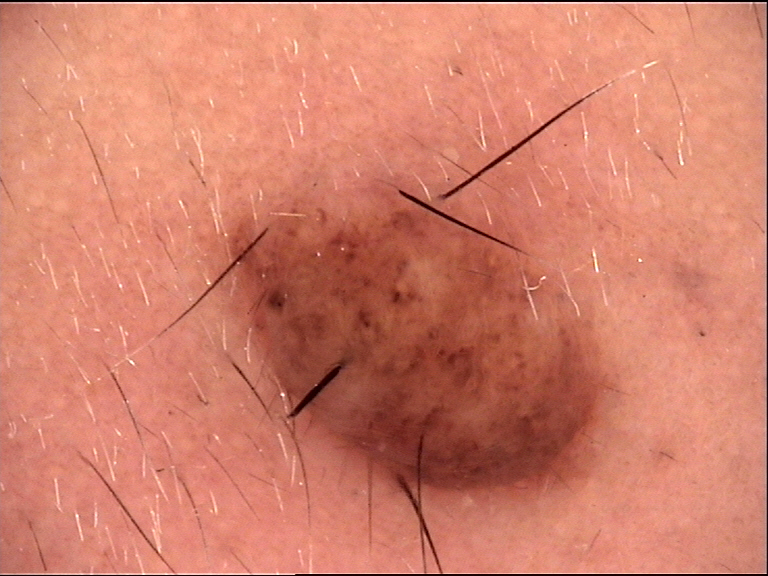A dermoscopy image of a single skin lesion. The diagnostic label was a banal lesion — a dermal nevus.